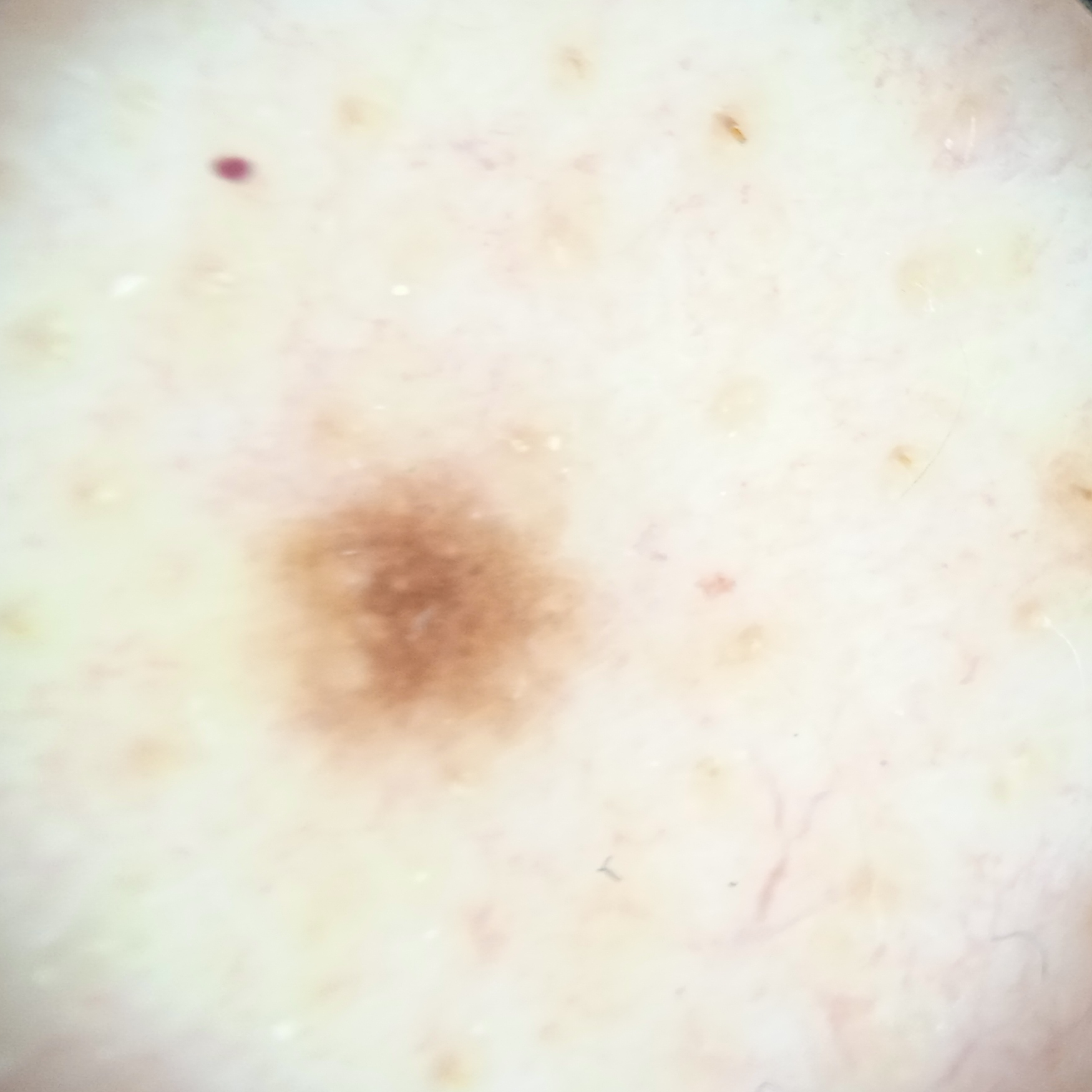diagnosis — melanocytic nevus (dermatologist consensus)